Female patient, age 50–59; located on the front of the torso and back of the torso; a close-up photograph: 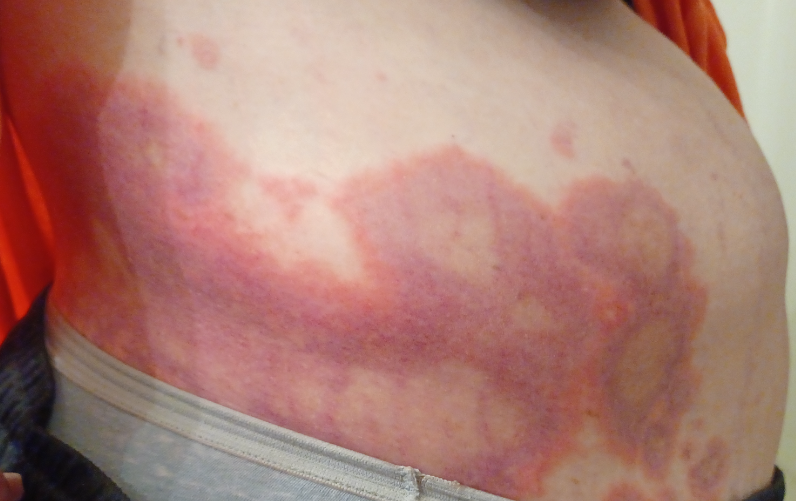Impression:
The skin condition could not be confidently assessed from this image.